A dermoscopy image of a single skin lesion — 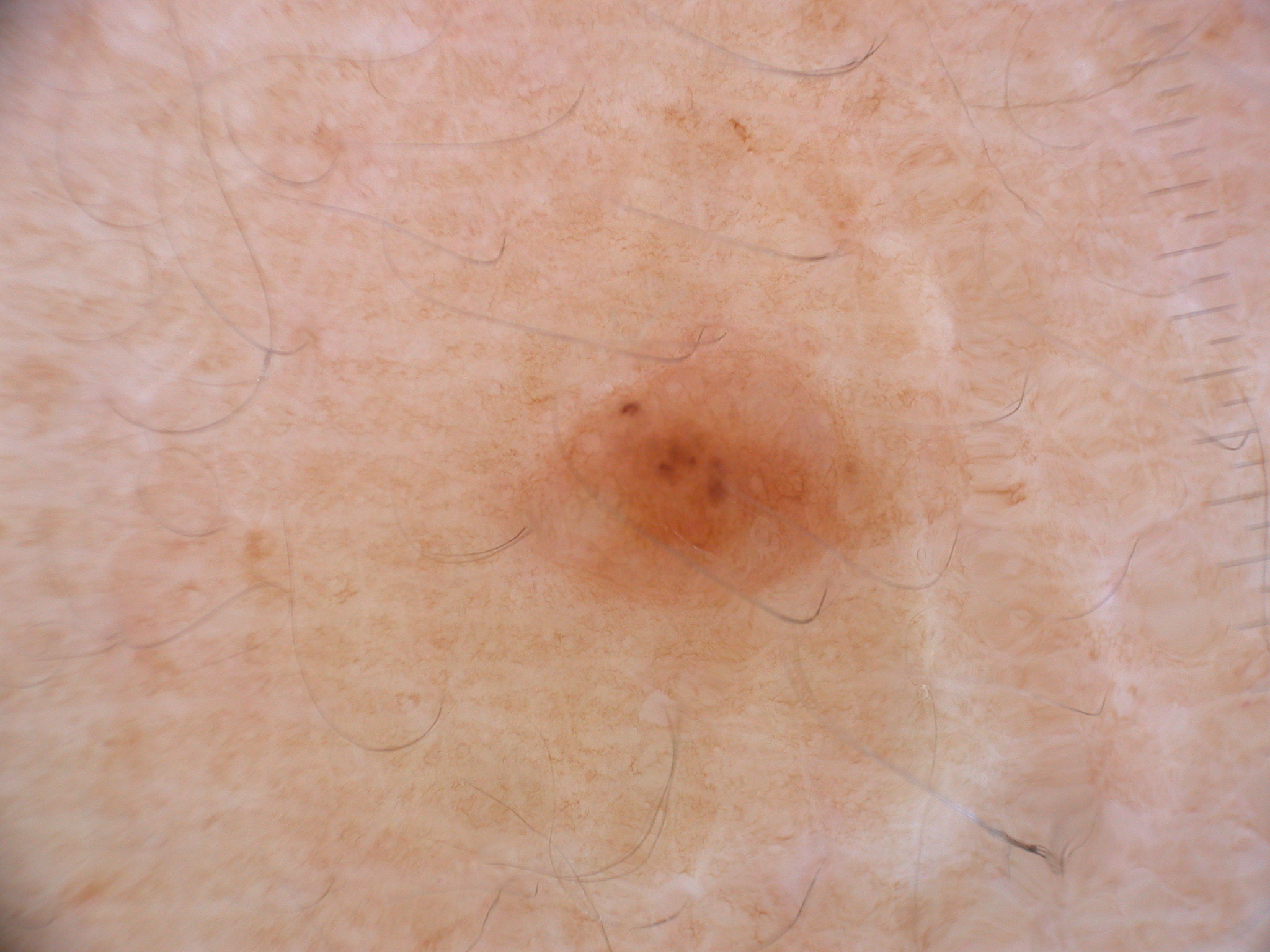Dermoscopically, the lesion shows pigment network. The lesion's extent is x1=506, y1=351, x2=914, y2=607. A small lesion within a wider field of skin. The diagnostic assessment was a melanocytic nevus, a benign skin lesion.